The subject is a male aged 70–79; a close-up photograph — 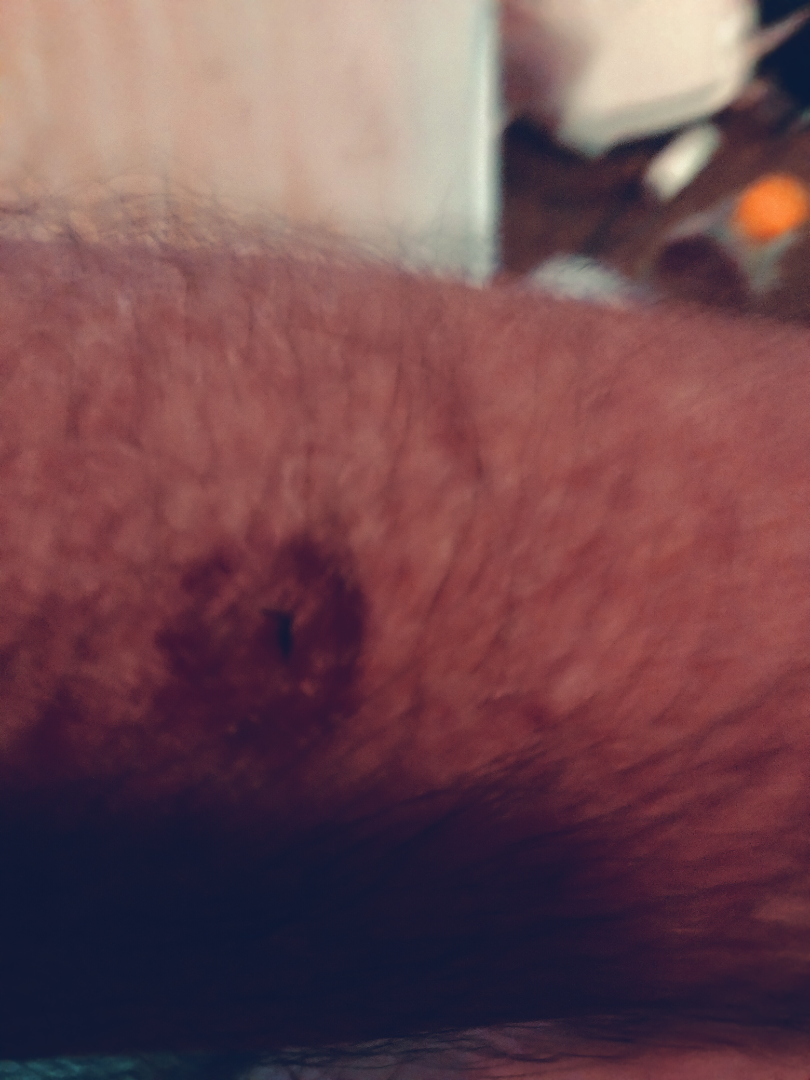Ecchymoses (1.00).